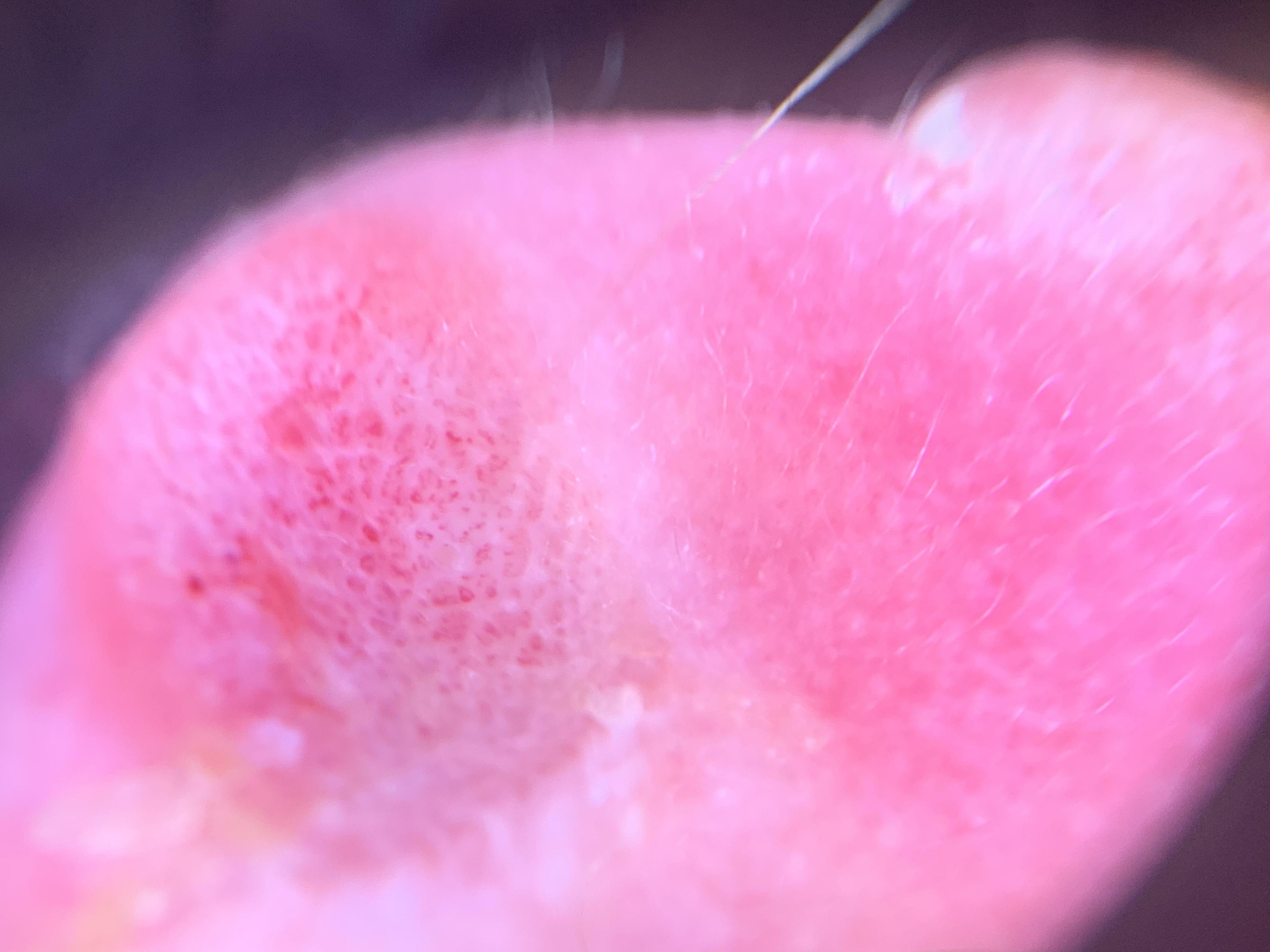Histopathologically confirmed as a squamous cell carcinoma.